The arm, head or neck, top or side of the foot, back of the hand, leg, front of the torso and back of the torso are involved; the photograph is a close-up of the affected area: 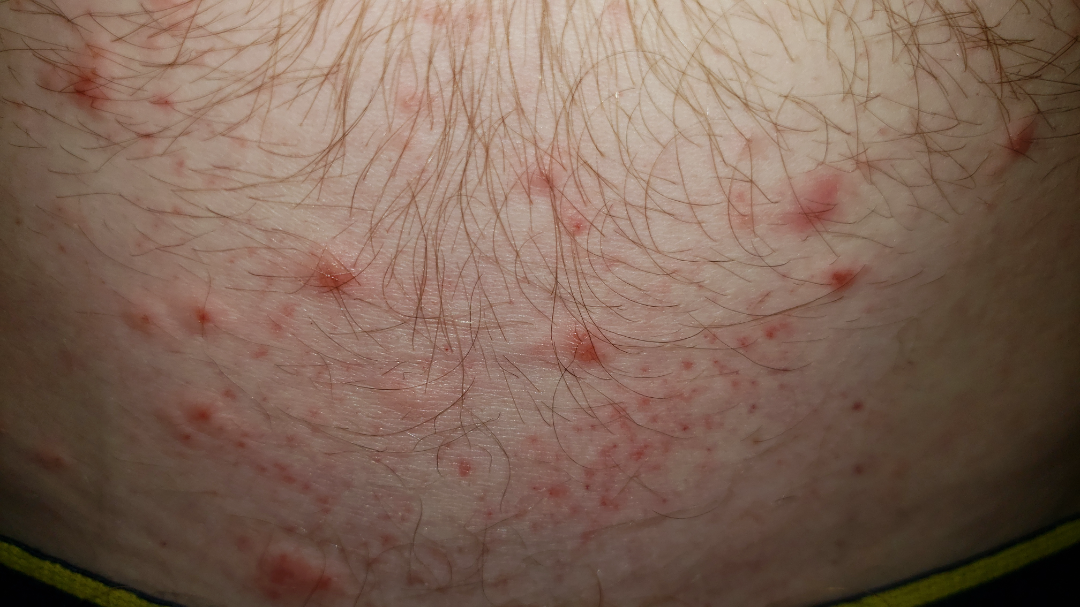{
  "assessment": "unable to determine",
  "patient_category": "a rash",
  "texture": [
    "raised or bumpy",
    "rough or flaky"
  ],
  "systemic_symptoms": "none reported",
  "duration": "more than one year",
  "skin_tone": {
    "fitzpatrick": "II"
  }
}